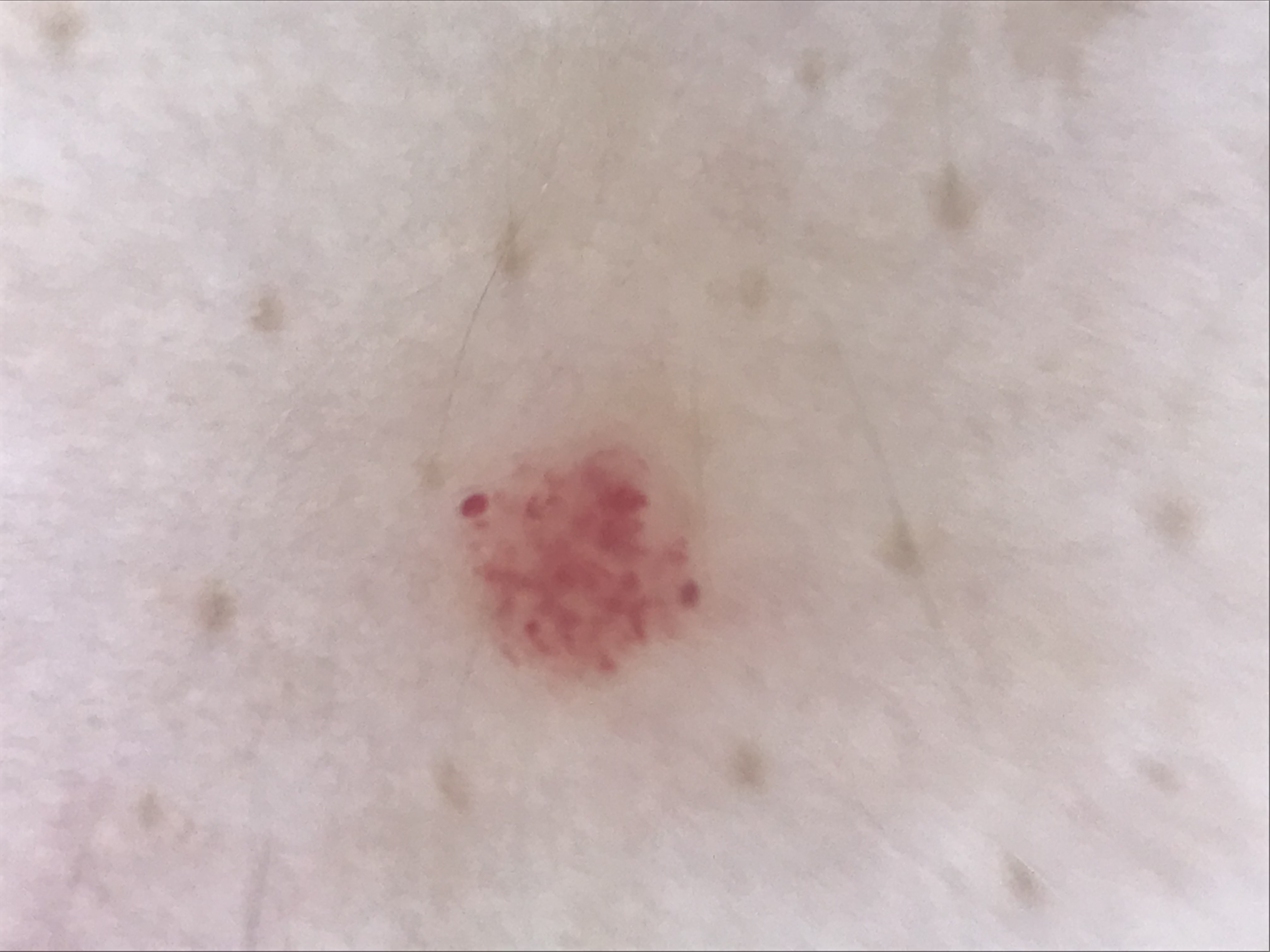A skin lesion imaged with a dermatoscope. The diagnostic label was a benign, vascular lesion — a hemangioma.